A dermoscopic close-up of a skin lesion.
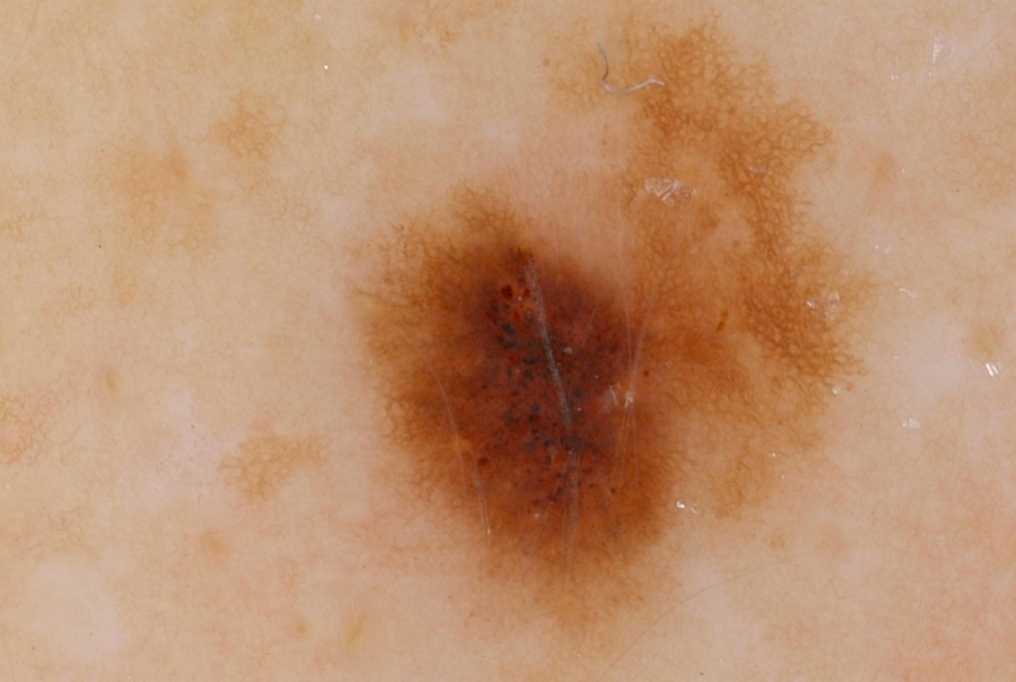Q: How much of the field does the lesion occupy?
A: ~34% of the field
Q: Which dermoscopic features were noted?
A: globules and pigment network
Q: What is notable about the lesion's margin?
A: clipped at the frame edge
Q: Where is the lesion in the image?
A: [343,0,880,677]
Q: What did the assessment conclude?
A: a melanoma, a malignant skin lesion